The lesion is associated with burning and darkening · FST II; non-clinician graders estimated Monk Skin Tone 1–2 · the contributor reports the condition has been present for one to three months · the photograph was taken at an angle · the patient also reports mouth sores:
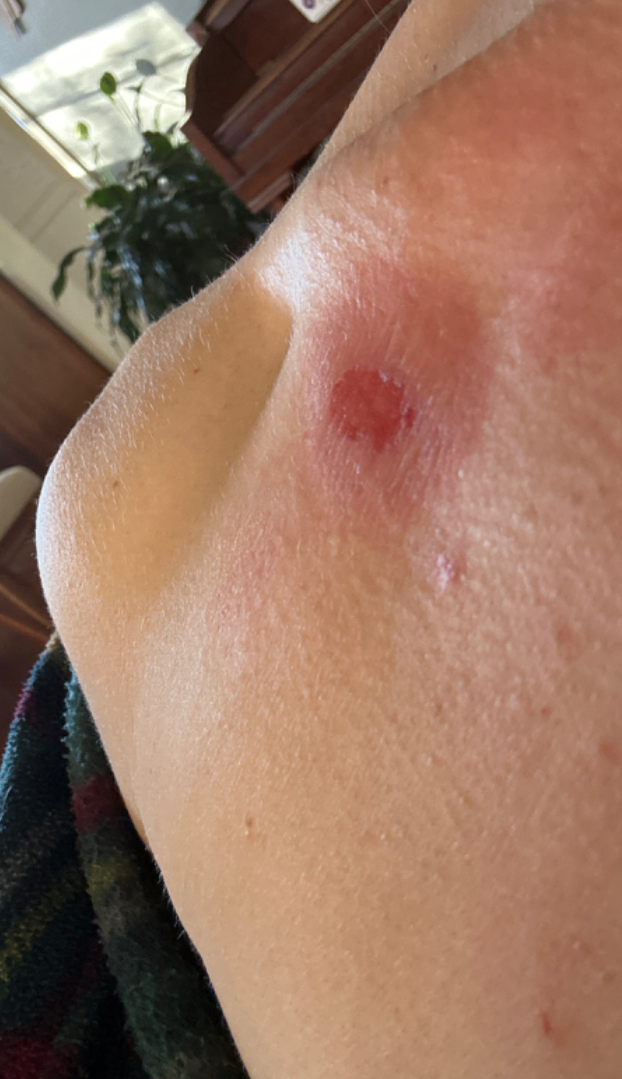Q: What conditions are considered?
A: most consistent with Insect Bite; also consider Blister